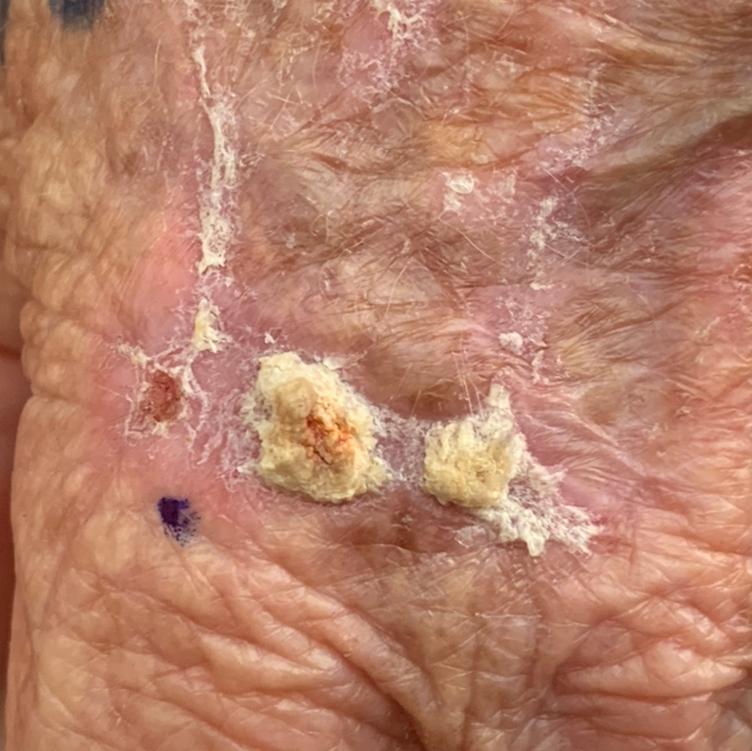modality = smartphone clinical photo | FST = II | risk factors = no prior malignancy (patient or family), no prior skin cancer (patient or family) | patient = female, aged 84 | site = a hand | diameter = approx. 26 × 10 mm | symptoms = elevation / no change in appearance, no bleeding | diagnosis = basal cell carcinoma (biopsy-proven).